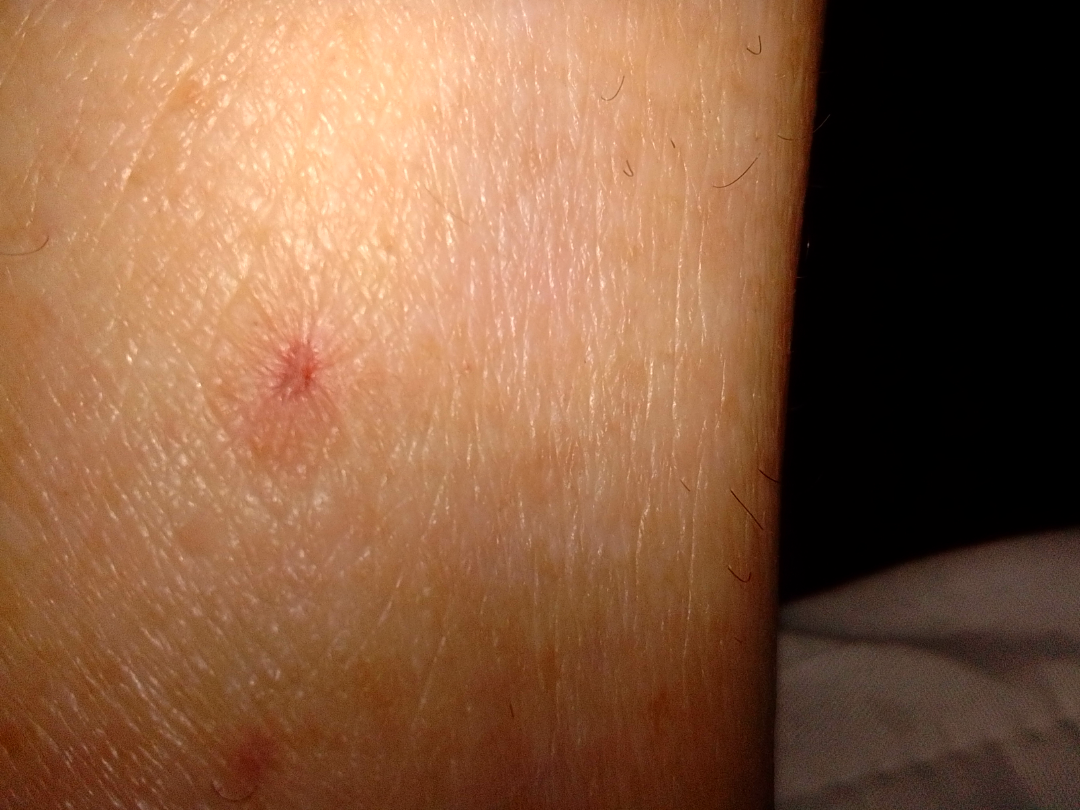Background:
The patient notes associated fatigue, shortness of breath, fever, mouth sores, chills and joint pain. The patient described the issue as a rash. Reported duration is one to four weeks. The photograph was taken at a distance.
Findings:
Consistent with Insect Bite.